The leg is involved · the patient notes the lesion is flat · female contributor, age 50–59 · the lesion is associated with bothersome appearance · a close-up photograph · present for about one day · the patient considered this a rash — 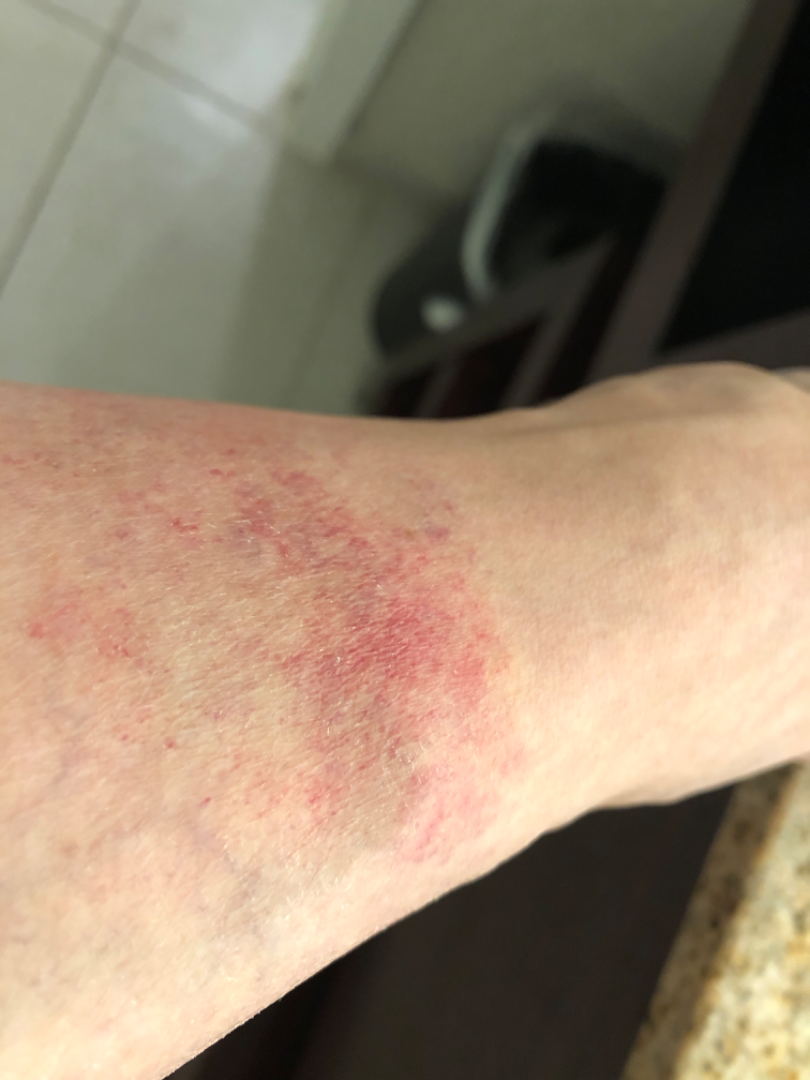| key | value |
|---|---|
| differential diagnosis | the leading consideration is Pigmented purpuric eruption; possibly Eczema; an alternative is Stasis Dermatitis |